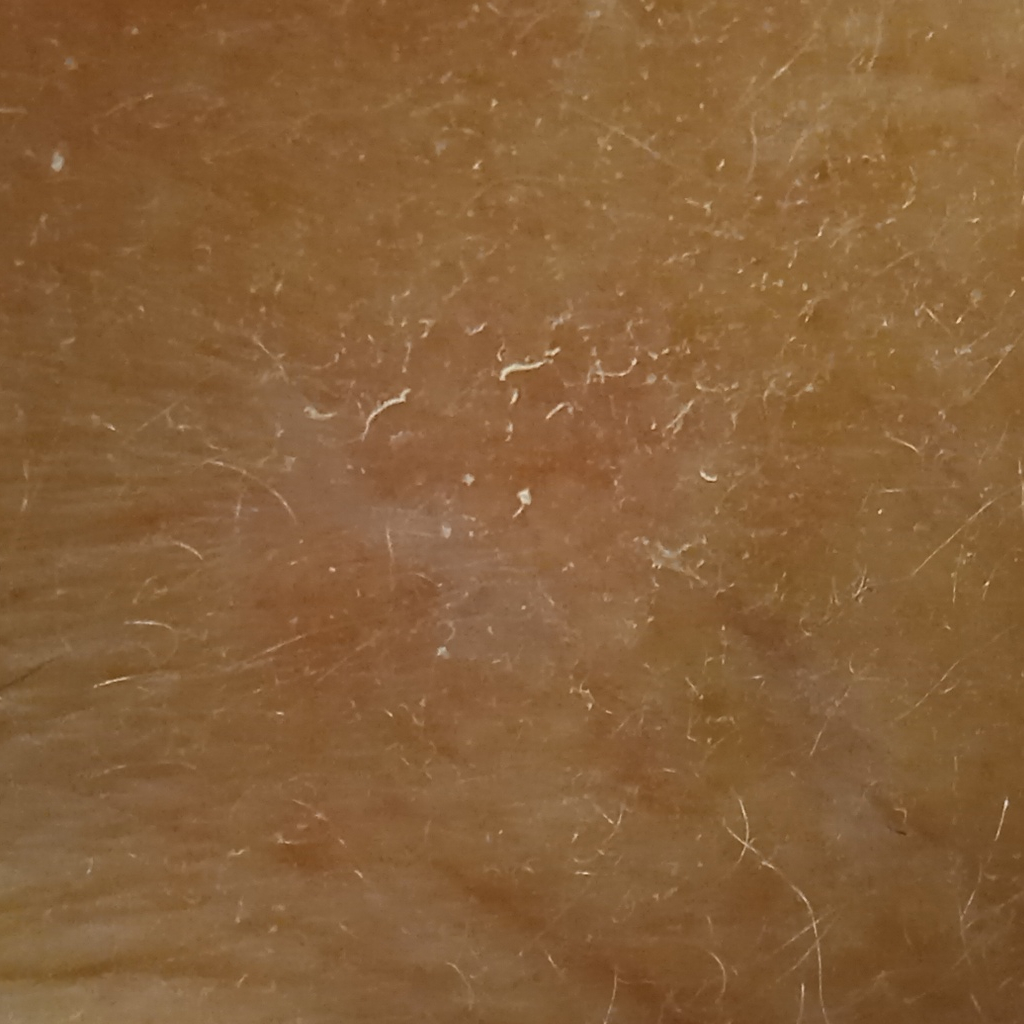image: clinical photograph
sun reaction: skin tans without first burning
risk factors: a family history of skin cancer, a personal history of cancer
referral context: clinical suspicion of basal cell carcinoma
subject: female, age 92
site: the face
size: 11.5 mm
pathology: basal cell carcinoma (biopsy-proven)